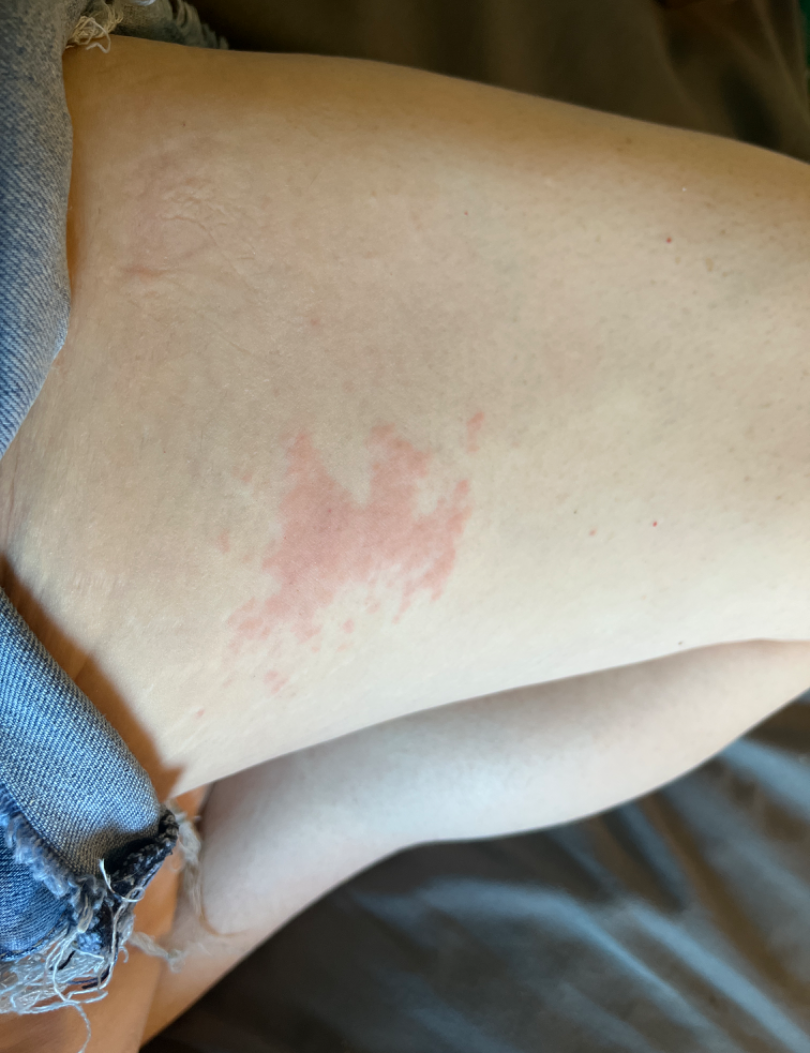<summary>
<skin_tone>
  <fitzpatrick>III</fitzpatrick>
  <monk_skin_tone>2</monk_skin_tone>
</skin_tone>
<shot_type>close-up</shot_type>
<differential>
  <tied_lead>Acute dermatitis, NOS; Irritant Contact Dermatitis</tied_lead>
</differential>
</summary>